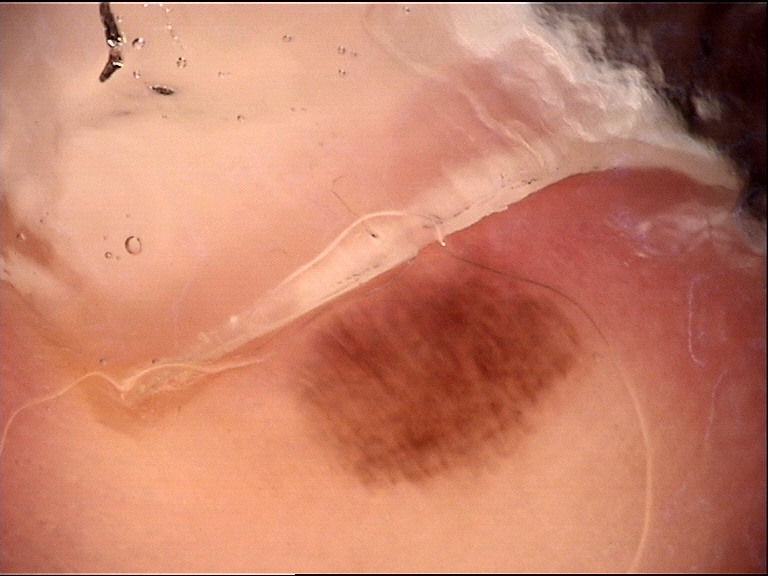A skin lesion imaged with a dermatoscope. Consistent with an acral junctional nevus.